The photo was captured at an angle — 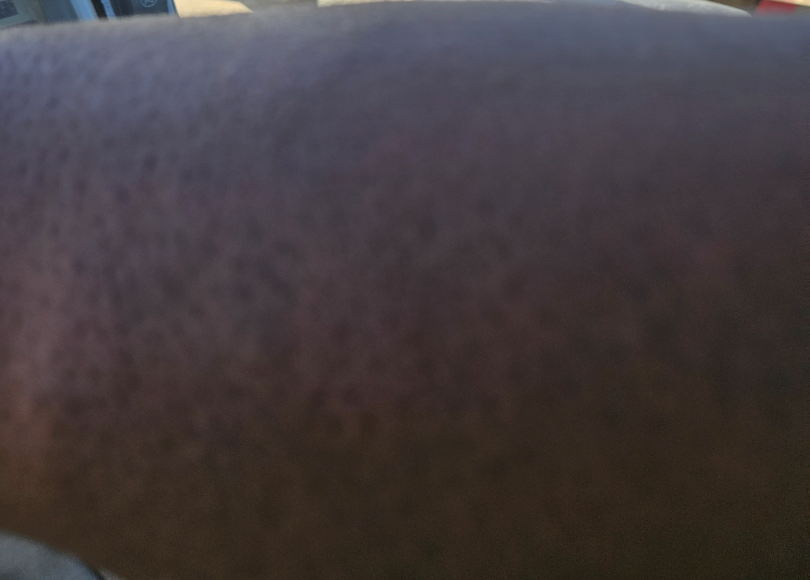Review: The reviewing dermatologist was unable to assign a differential diagnosis from the image.